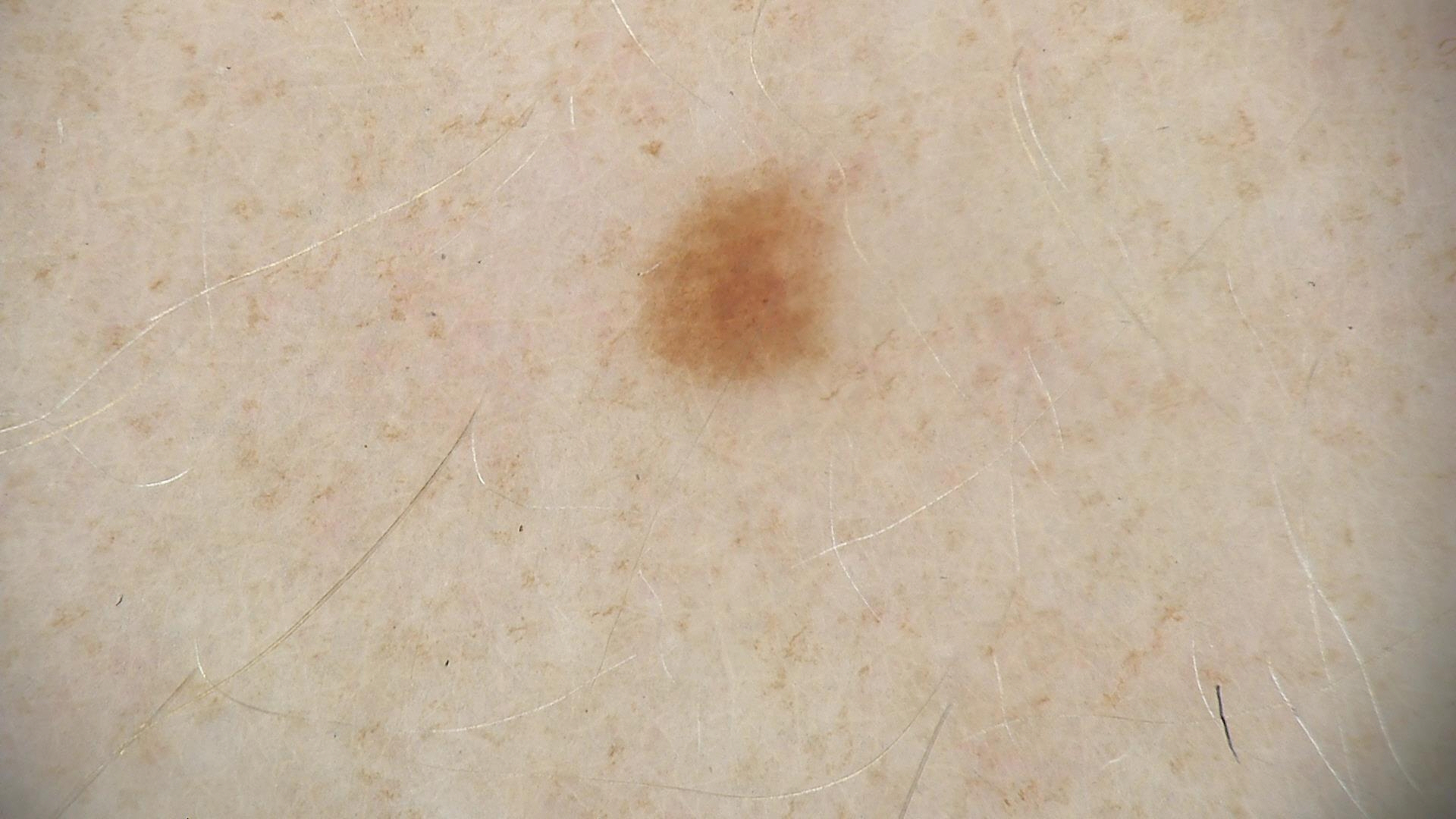image: dermatoscopy
diagnosis:
  name: dysplastic junctional nevus
  code: jd
  malignancy: benign
  super_class: melanocytic
  confirmation: expert consensus